A dermoscopy image of a single skin lesion.
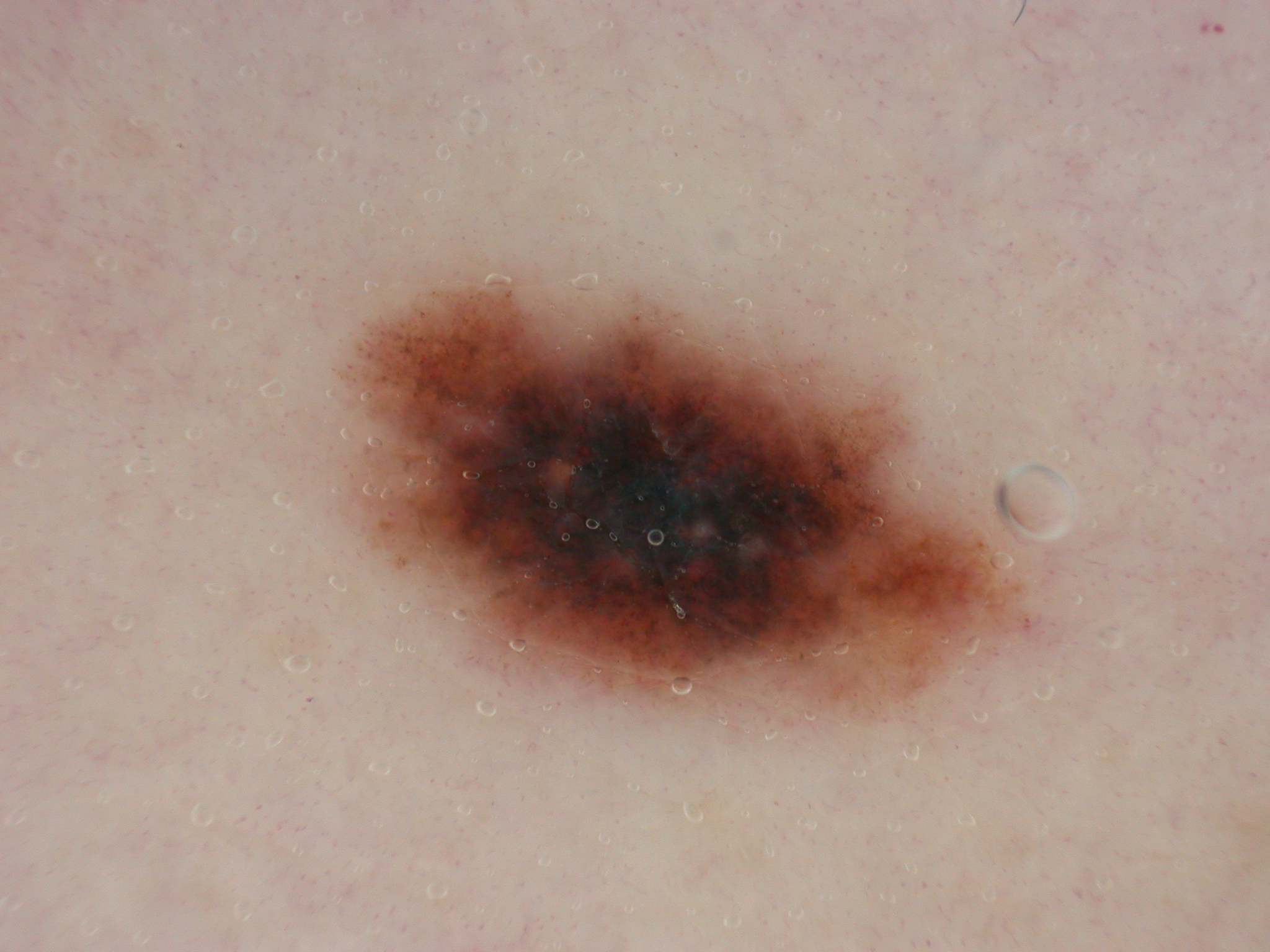{"lesion_location": {"bbox_xyxy": [327, 285, 1029, 708]}, "diagnosis": {"name": "melanoma", "malignancy": "malignant", "lineage": "melanocytic", "provenance": "histopathology"}}